The photograph is a close-up of the affected area: 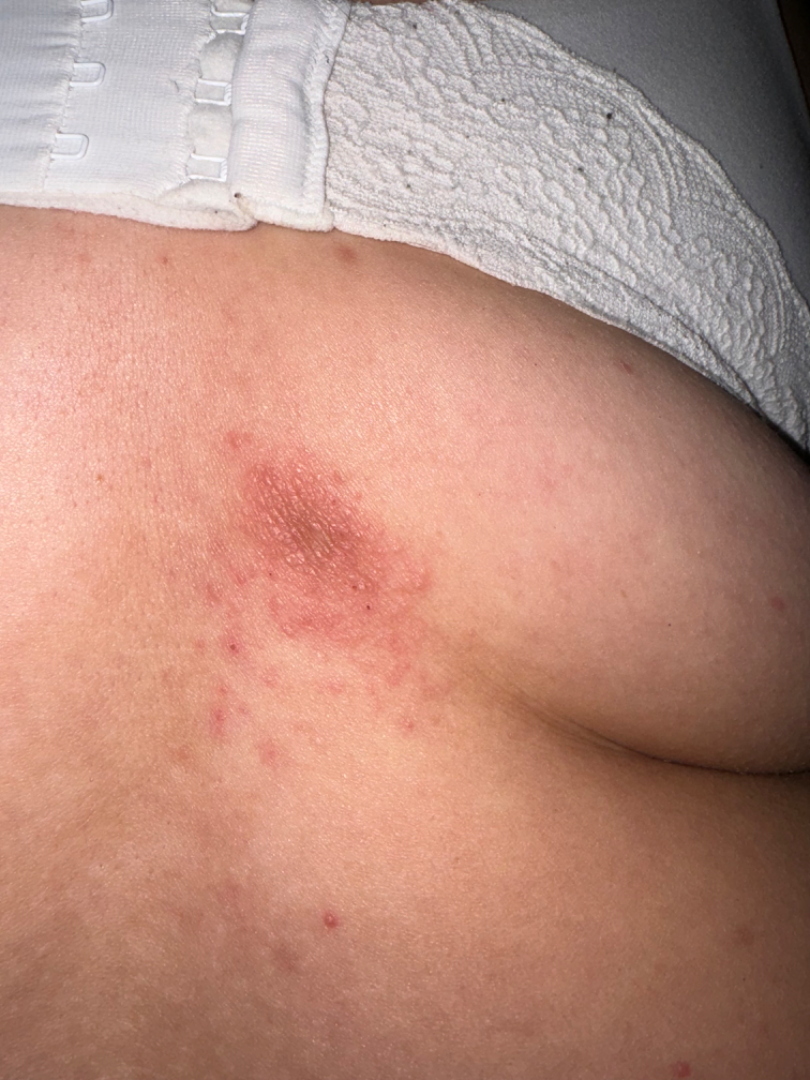On remote review of the image: the primary impression is Lichen Simplex Chronicus; also raised was Irritant Contact Dermatitis; a more distant consideration is Drug Rash.